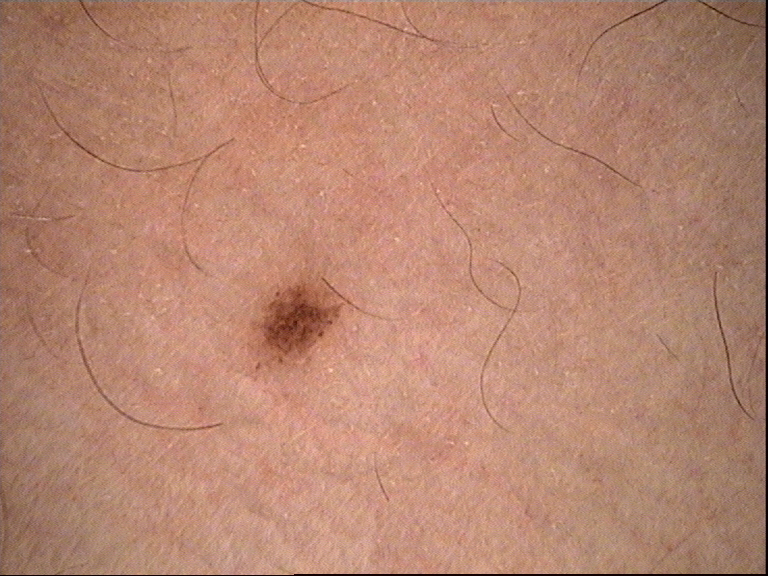A dermoscopic close-up of a skin lesion.
The diagnostic label was a dysplastic junctional nevus.